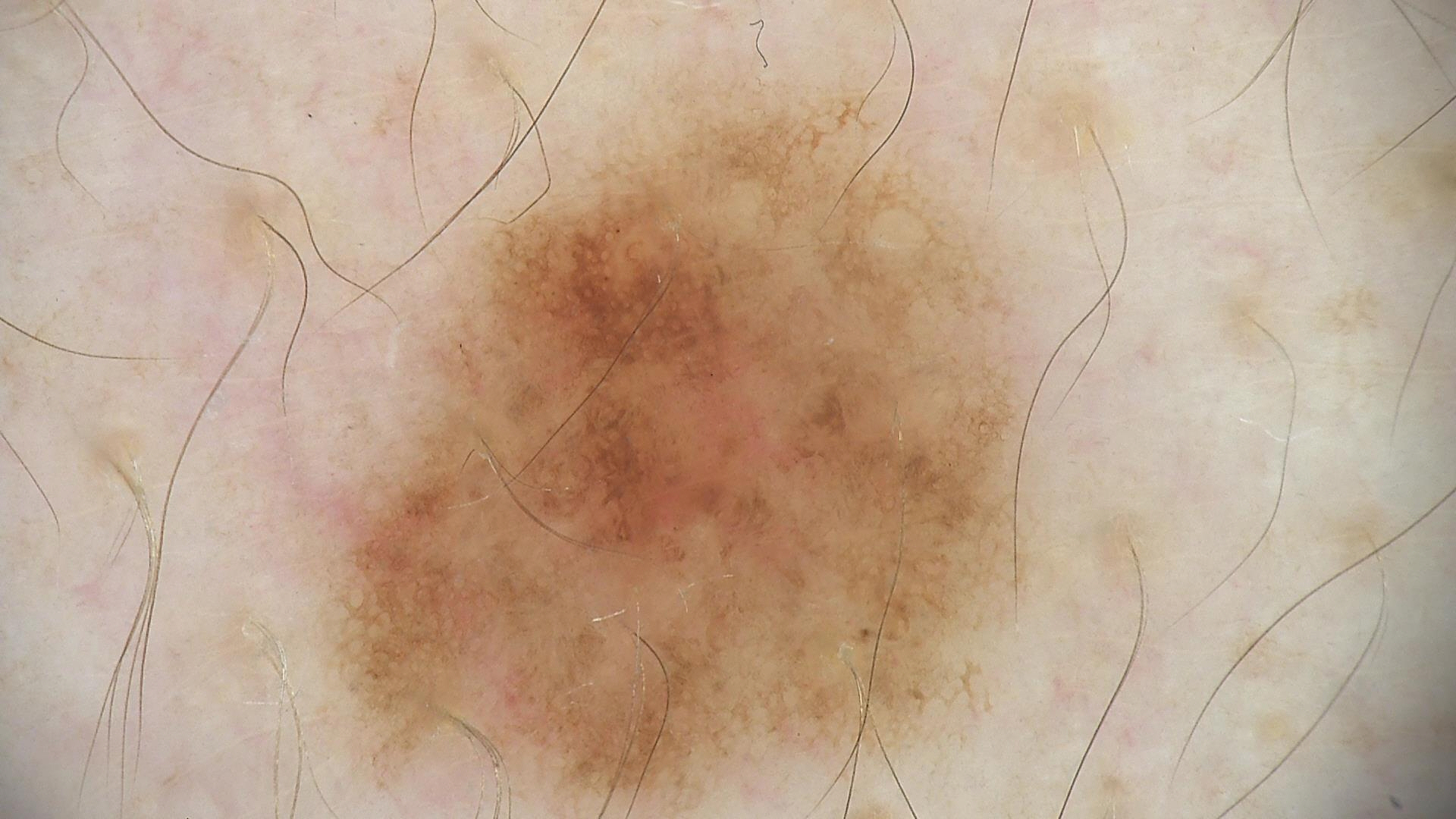The diagnostic label was a dysplastic junctional nevus.